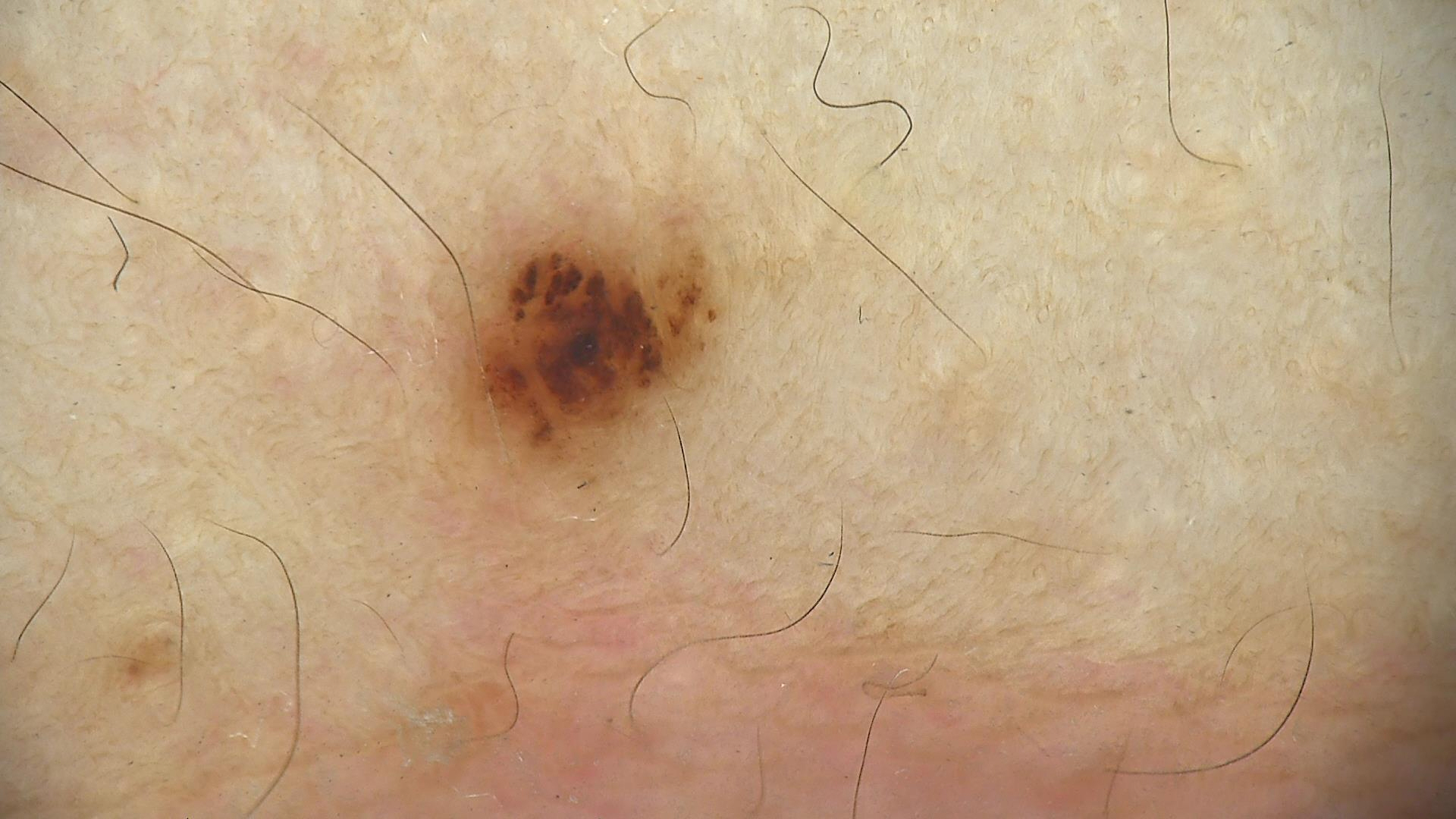- image: dermoscopy
- class: dysplastic junctional nevus (expert consensus)